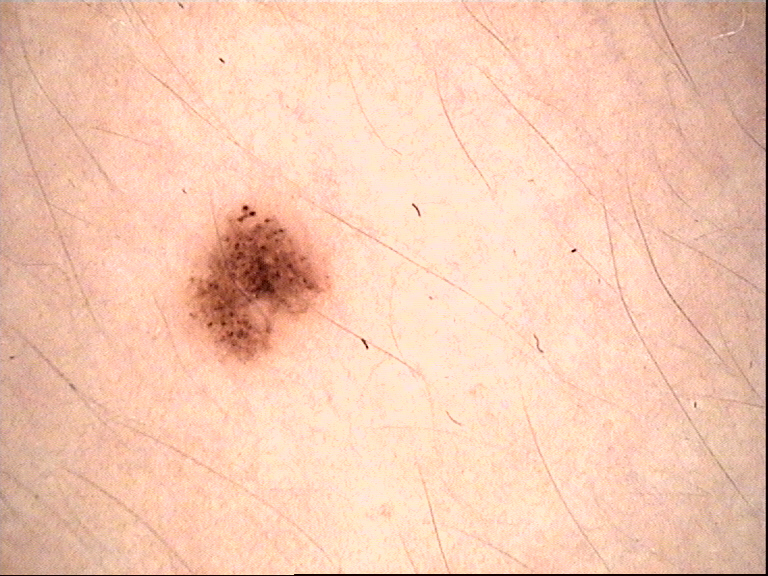diagnosis = dysplastic junctional nevus (expert consensus).